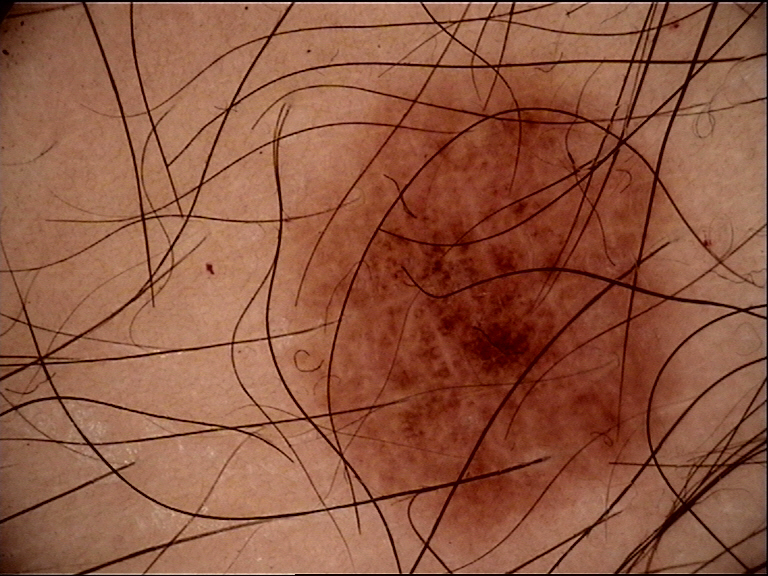  diagnosis:
    name: dysplastic junctional nevus
    code: jd
    malignancy: benign
    super_class: melanocytic
    confirmation: expert consensus